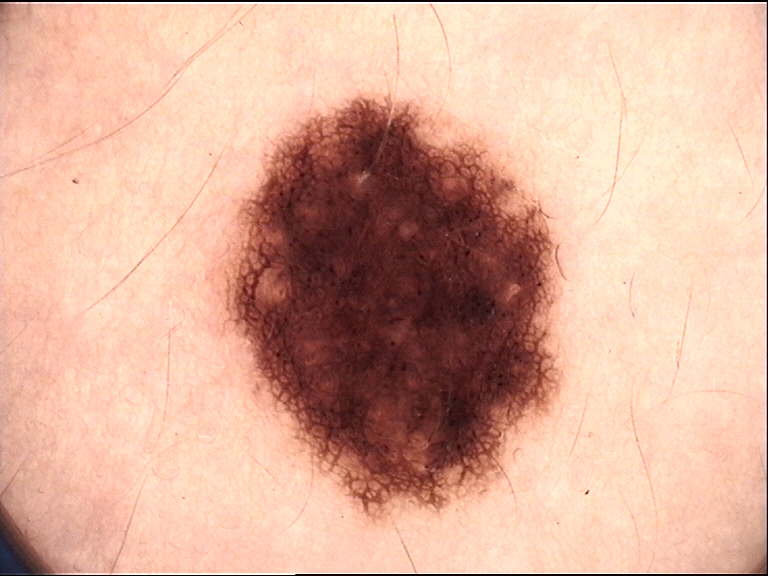Q: What is the diagnosis?
A: dysplastic junctional nevus (expert consensus)